Dermoscopy of a skin lesion.
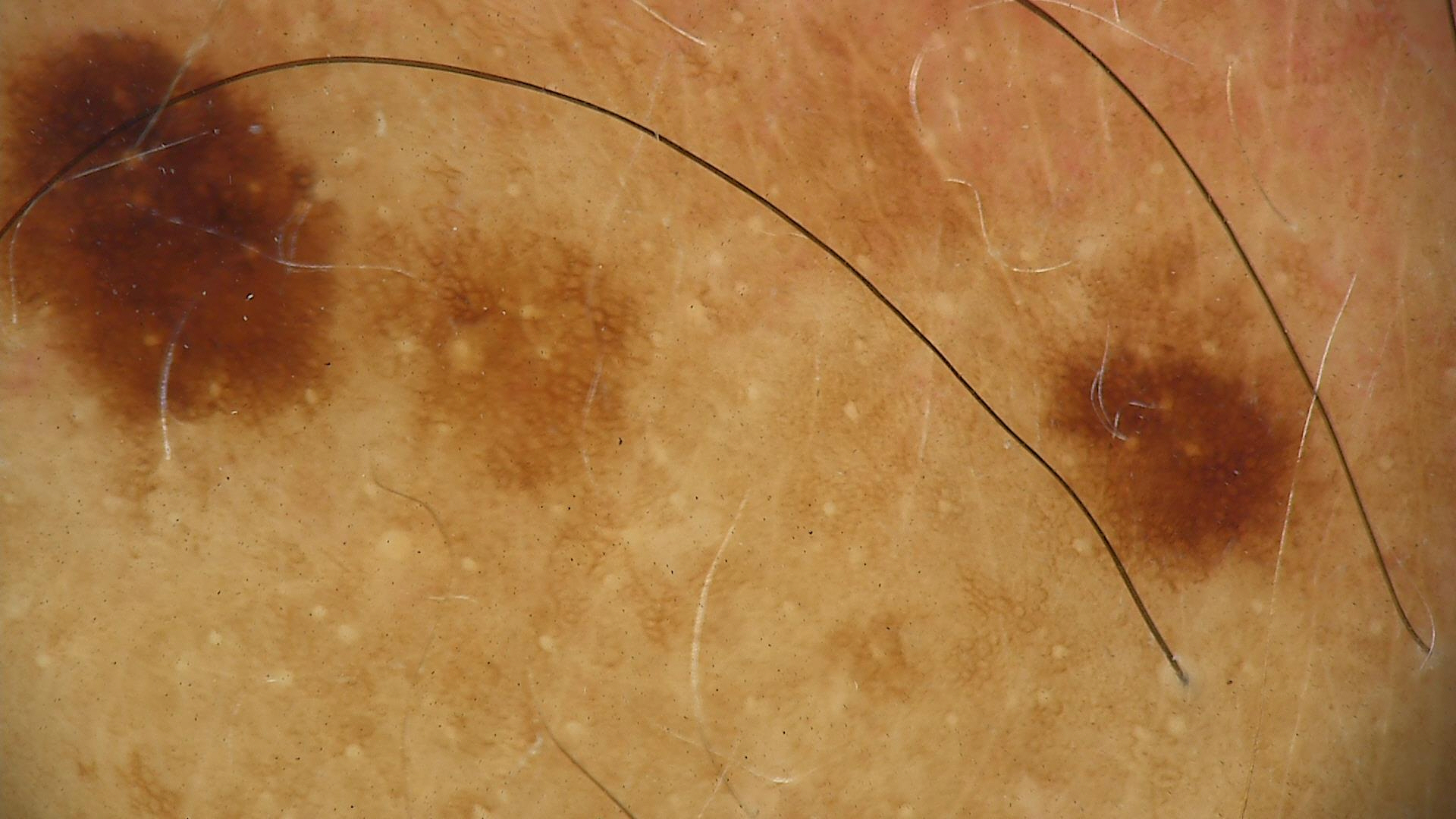- label — dysplastic junctional nevus (expert consensus)